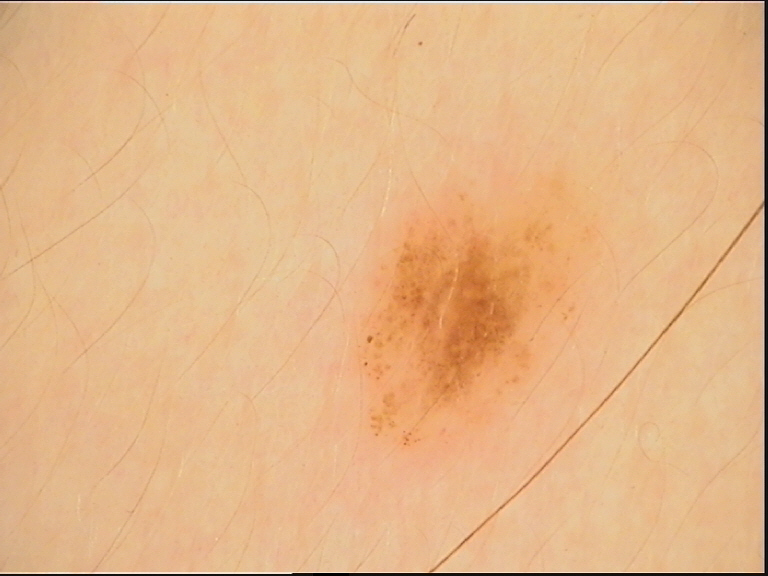Conclusion:
Diagnosed as a dysplastic junctional nevus.